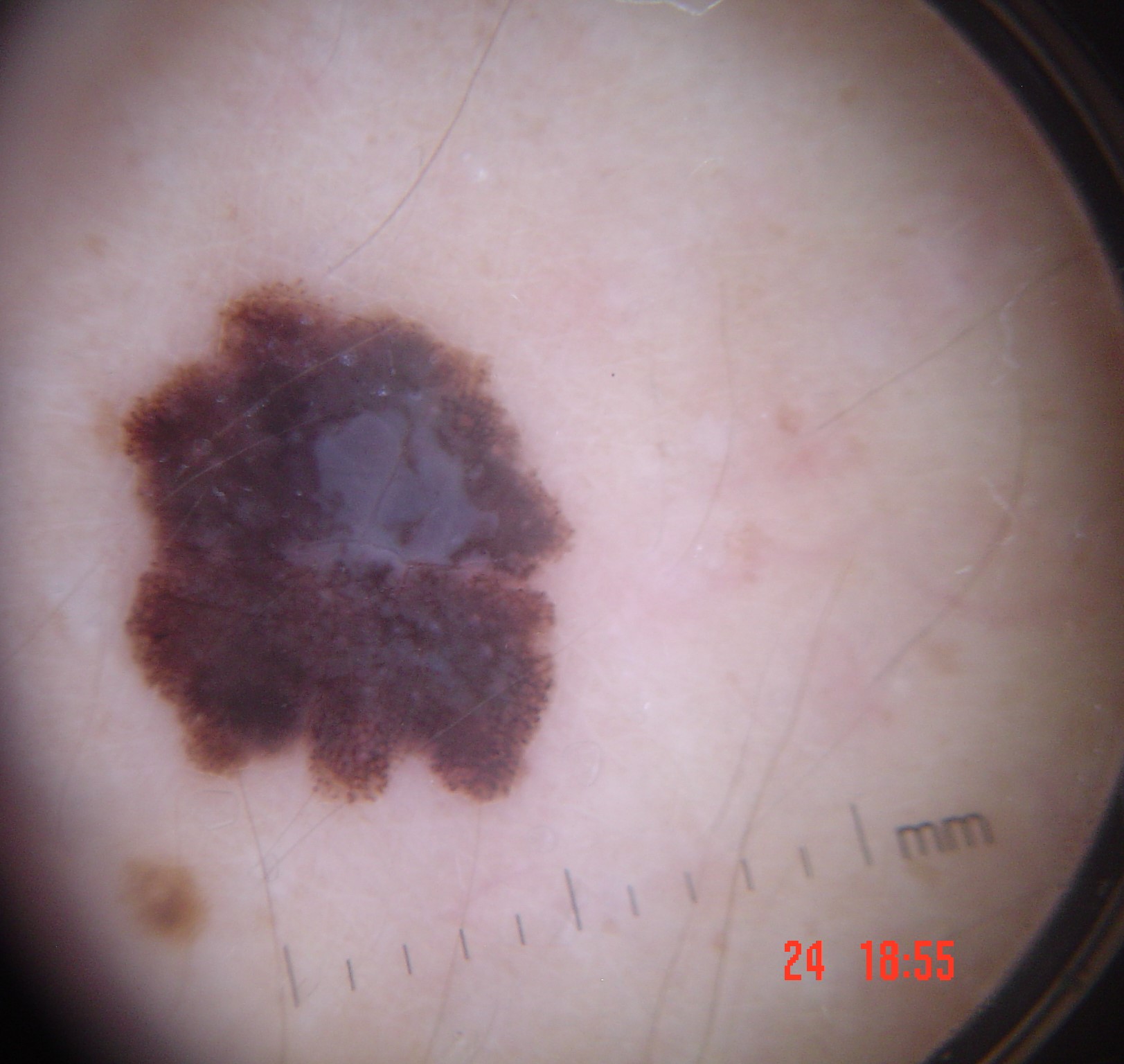Findings: A dermoscopic image of a skin lesion. Diagnosis: Histopathology confirmed a melanoma.